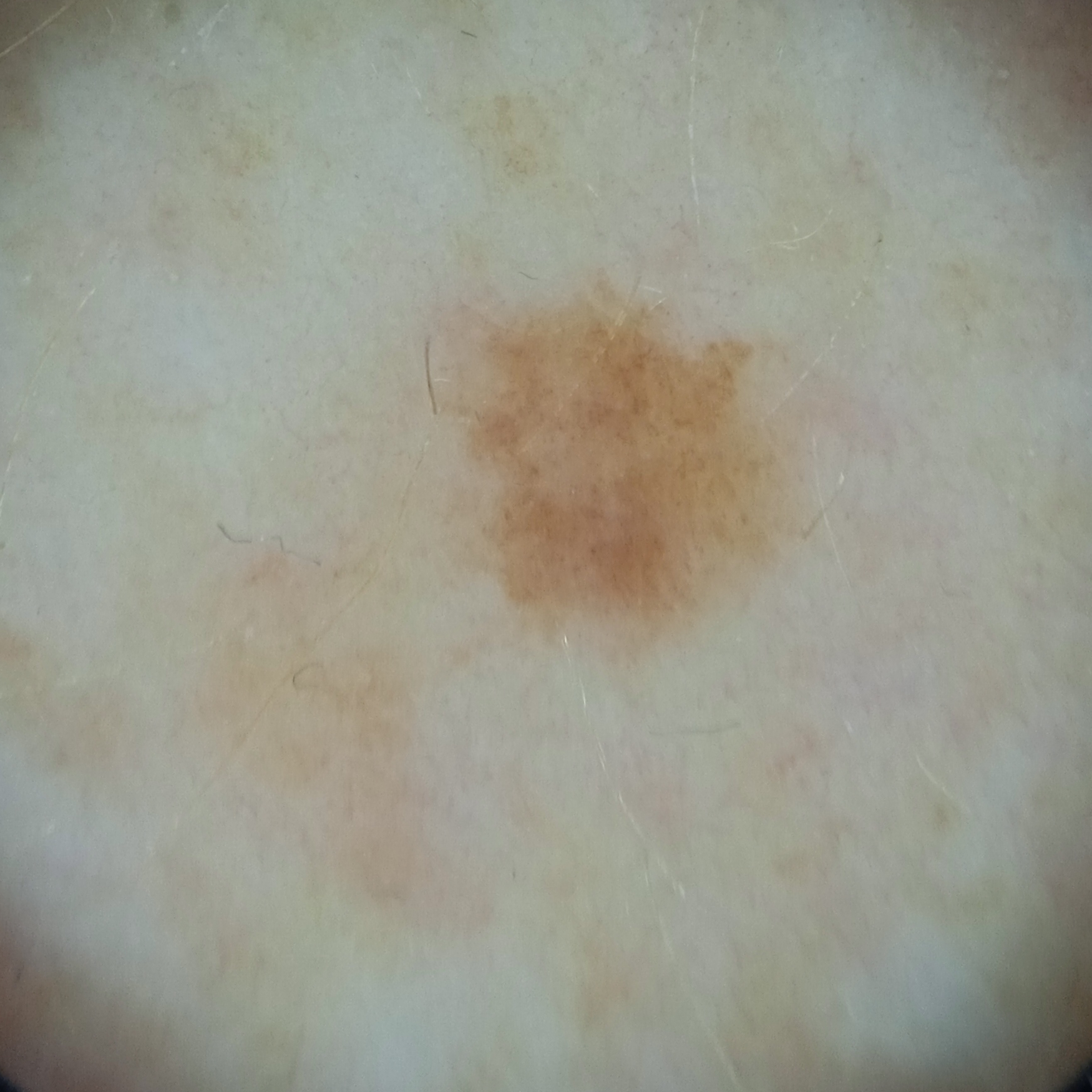The patient describes having a moderate number of moles.
A female subject 53 years old.
The patient says their skin reddens with sun exposure.
Collected as part of a research study, without a referral diagnosis.
The lesion involves a leg.
Reviewed by four dermatologists, the consensus diagnosis was a melanocytic nevus; the four reviewers were unanimous.